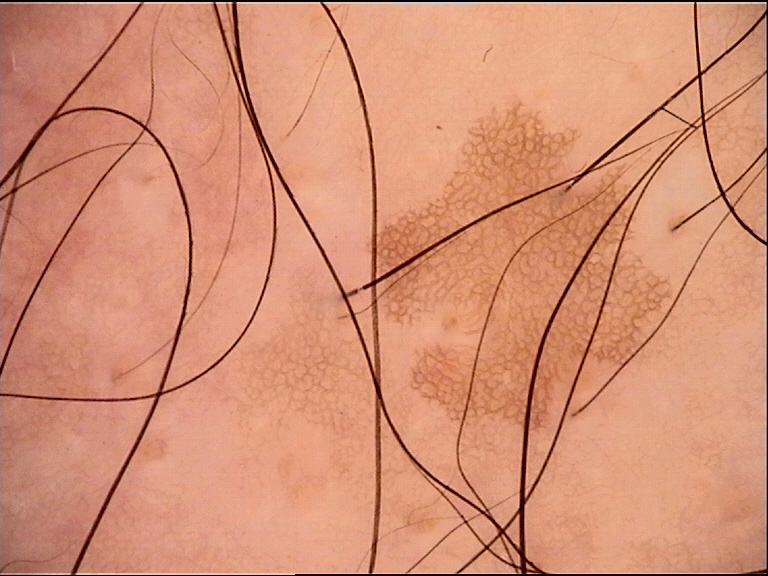imaging=dermatoscopy; diagnostic label=solar lentigo (expert consensus).